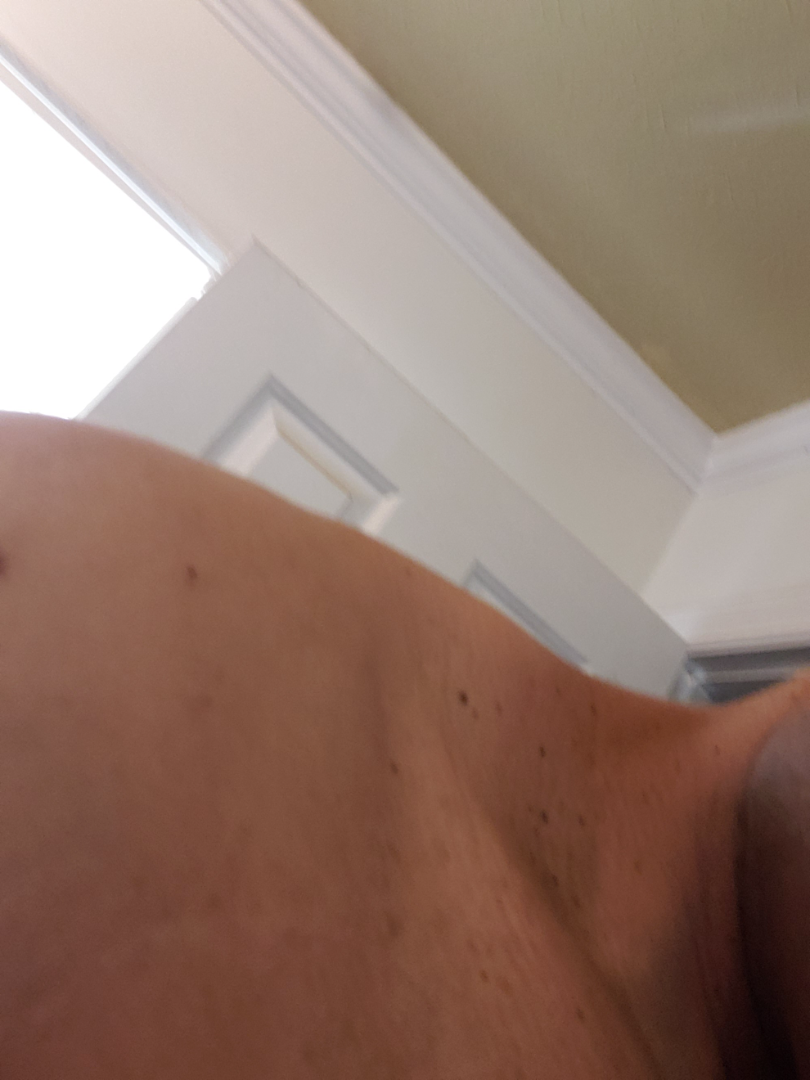The skin condition could not be confidently assessed from this image. Reported lesion symptoms include bothersome appearance. The affected area is the head or neck. The patient is a male aged 40–49. The condition has been present for more than five years. No associated systemic symptoms reported. Close-up view. The lesion is described as raised or bumpy. The patient considered this a growth or mole.